A skin lesion imaged with a dermatoscope.
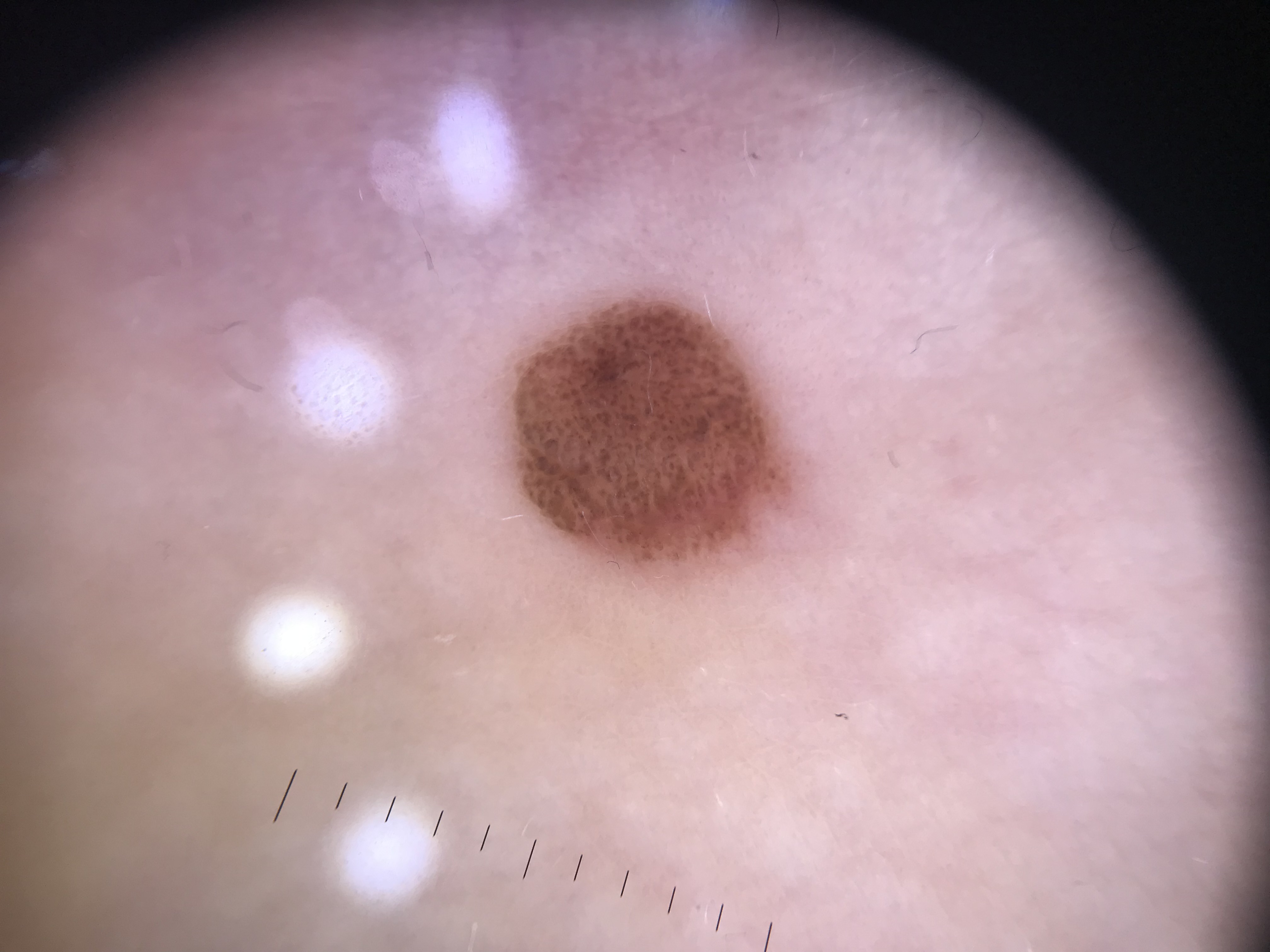Conclusion: Labeled as a banal lesion — a compound nevus.